A dermoscopic close-up of a skin lesion.
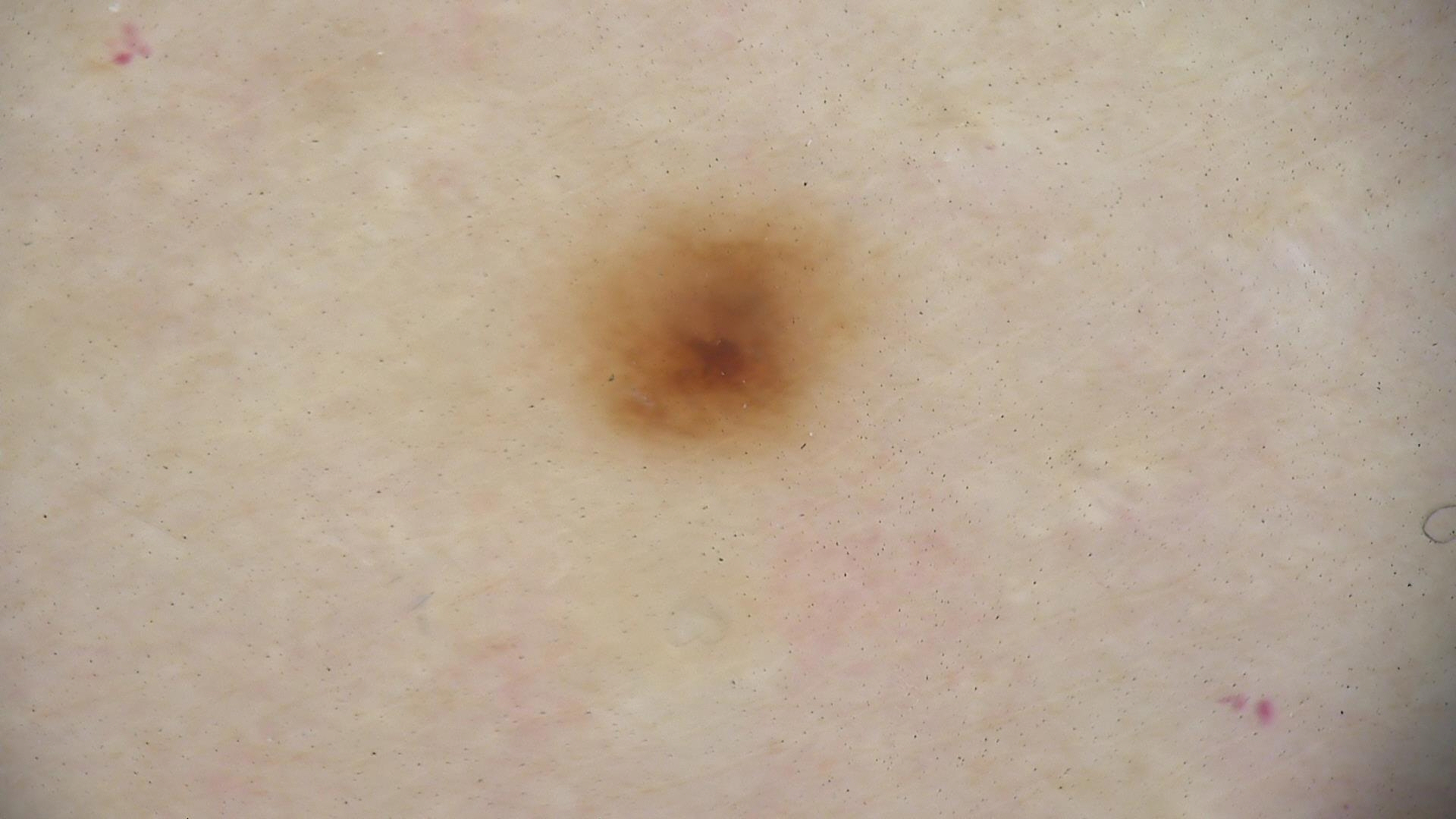The diagnosis was a dysplastic compound nevus.